The patient reports a personal history of cancer, a personal history of skin cancer, and no prior organ transplant. The patient says their skin reddens with sun exposure. The patient describes having a moderate number of moles. Collected as part of a research study, without a referral diagnosis. A clinical close-up of a skin lesion:
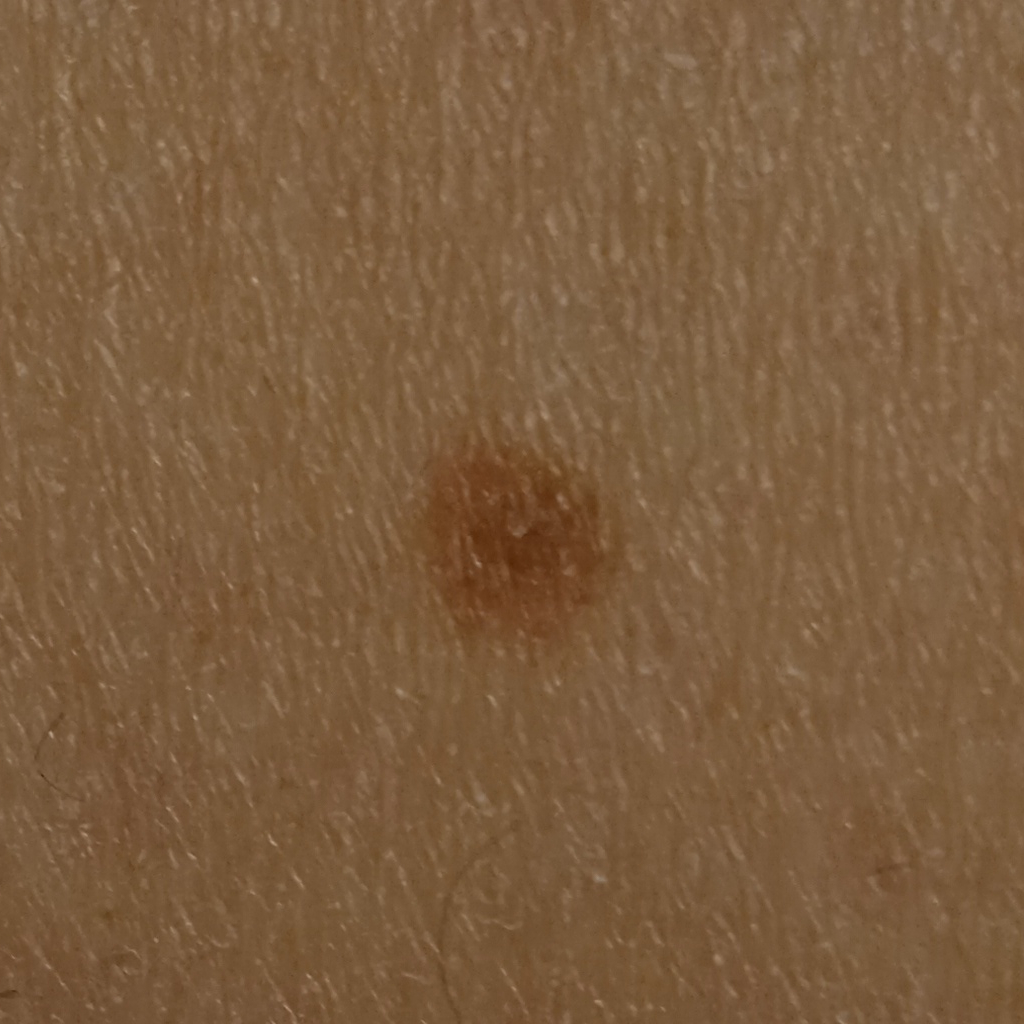Findings: The lesion measures approximately 4.1 mm. Conclusion: The diagnostic impression was a melanocytic nevus.